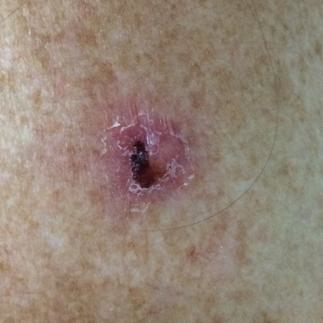image: smartphone clinical photo | exposures: prior malignancy (patient or family), pesticide exposure | body site: the back | lesion diameter: approx. 10 × 9 mm | symptoms: itching, elevation, pain, bleeding, growth | diagnostic label: basal cell carcinoma (biopsy-proven).